Reported lesion symptoms include itching · this image was taken at an angle · the lesion involves the arm · texture is reported as raised or bumpy and rough or flaky · the patient indicates the condition has been present for one to three months · the patient reported no systemic symptoms · the contributor is 40–49, male.
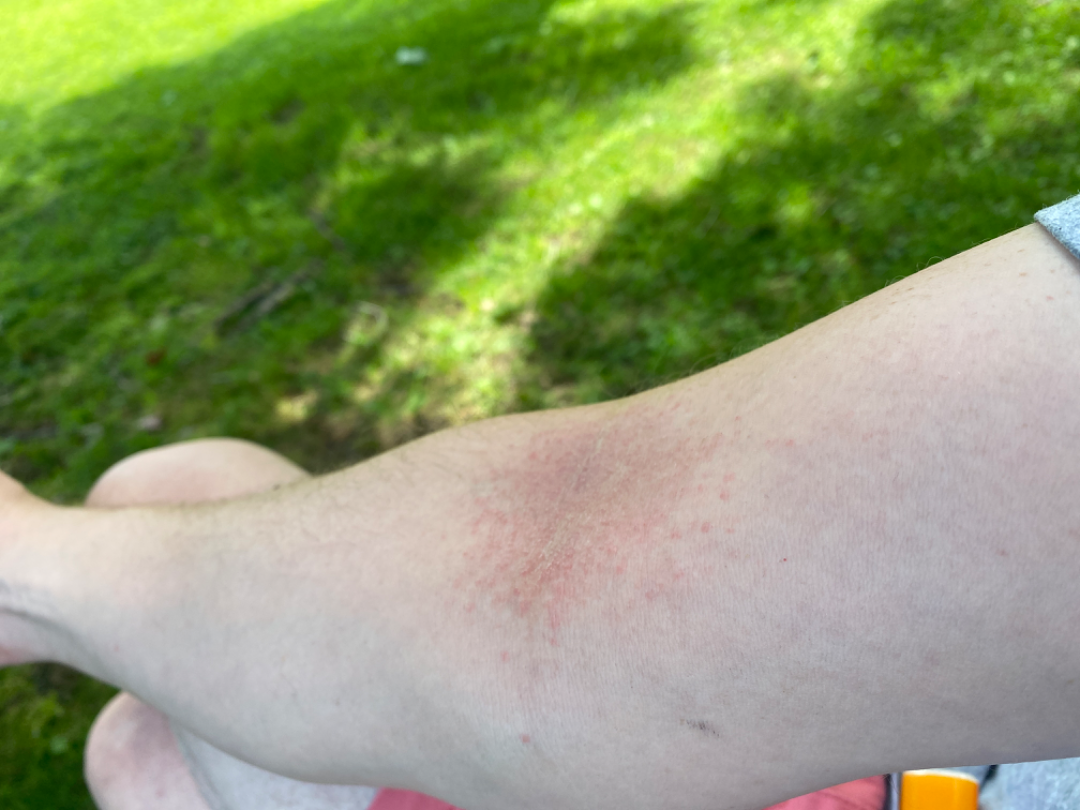On teledermatology review, in keeping with Eczema.